Close-up view, the lesion involves the arm and head or neck: 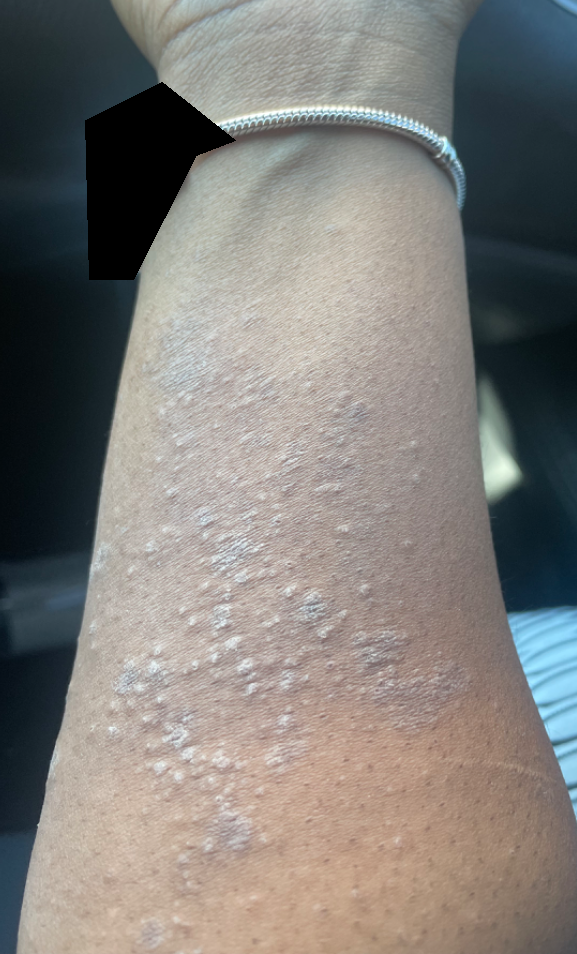History: The lesion is described as rough or flaky. The condition has been present for one to three months. Impression: The reviewing clinician's impression was: Eczema (most likely); Lichen planus/lichenoid eruption (possible).